The photograph was taken at a distance — 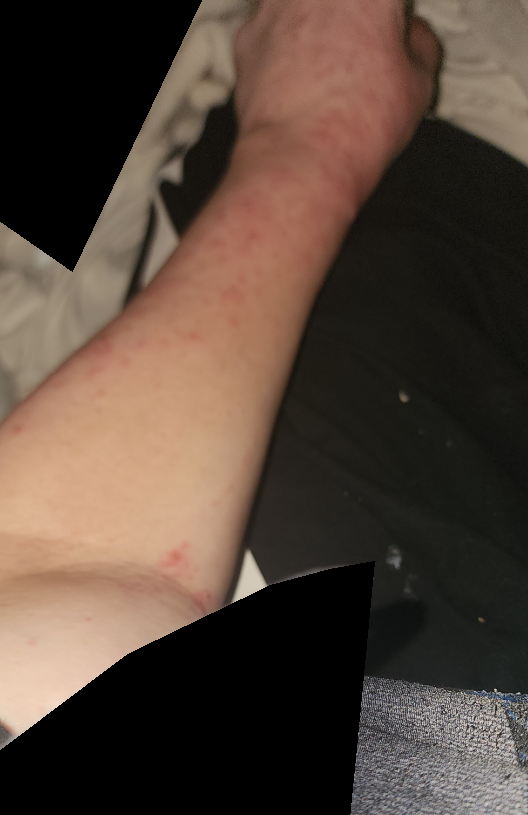The case was difficult to assess from the available photograph.